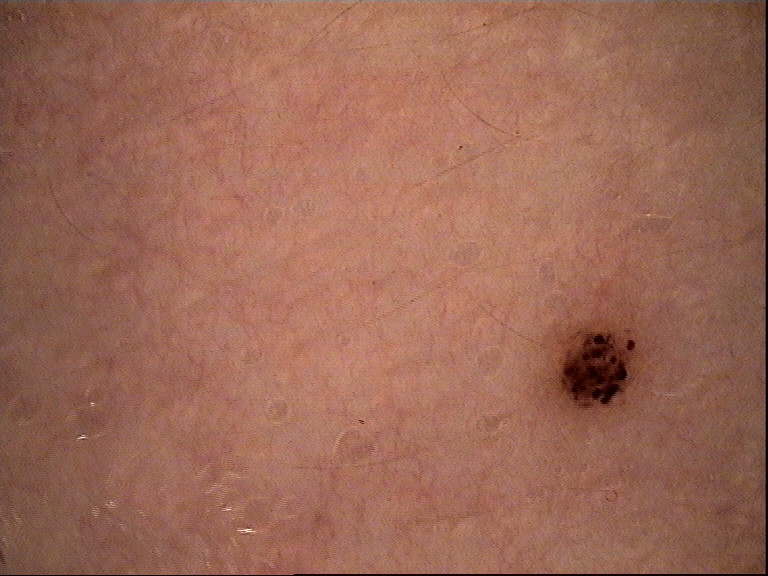The diagnosis was a benign lesion — a dysplastic junctional nevus.